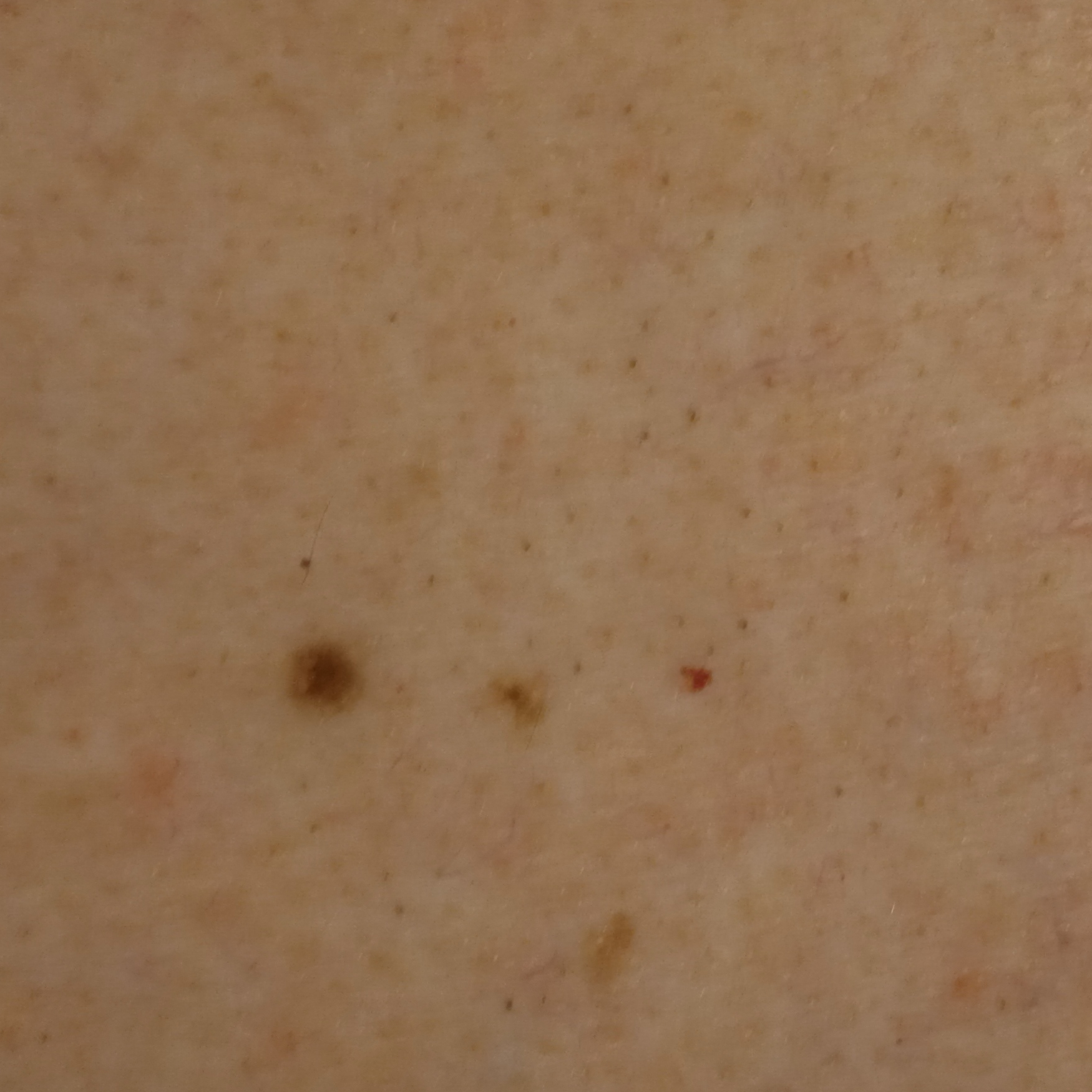patient = male, age 65; imaging = clinical photograph; anatomic site = the back; diameter = 3.6 mm; assessment = melanocytic nevus (dermatologist consensus).